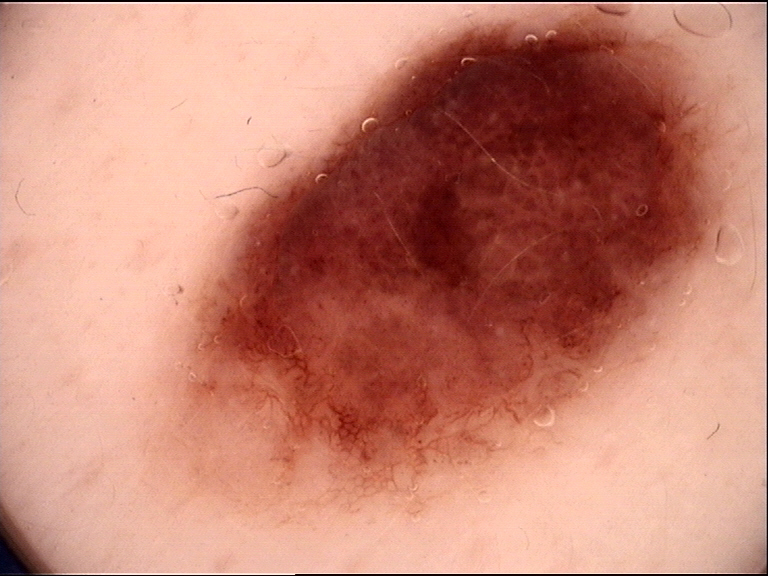A skin lesion imaged with a dermatoscope.
The diagnostic label was a dysplastic compound nevus.